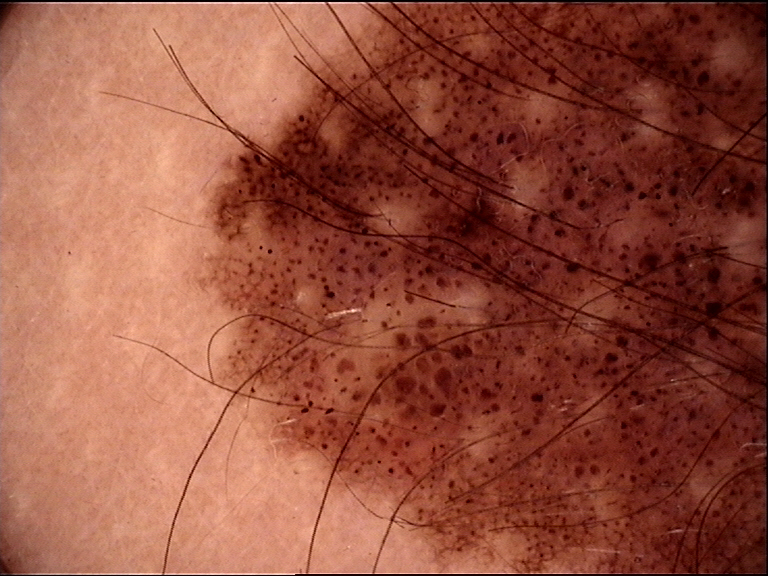Case:
- diagnostic label · congenital compound nevus (expert consensus)